A clinical close-up photograph of a skin lesion · the chart records prior skin cancer (patient or family) and no alcohol use · a female subject aged 44 · recorded as Fitzpatrick II: 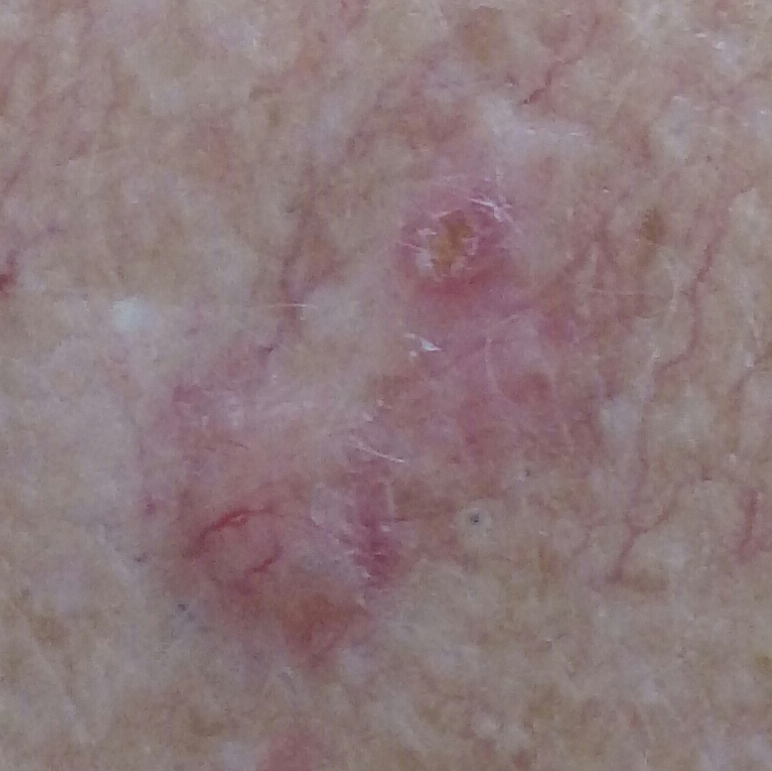<case>
<lesion_location>the chest</lesion_location>
<lesion_size>
<diameter_1_mm>16.0</diameter_1_mm>
<diameter_2_mm>7.0</diameter_2_mm>
</lesion_size>
<symptoms>
<present>elevation</present>
</symptoms>
<diagnosis>
<name>basal cell carcinoma</name>
<code>BCC</code>
<malignancy>malignant</malignancy>
<confirmation>histopathology</confirmation>
</diagnosis>
</case>